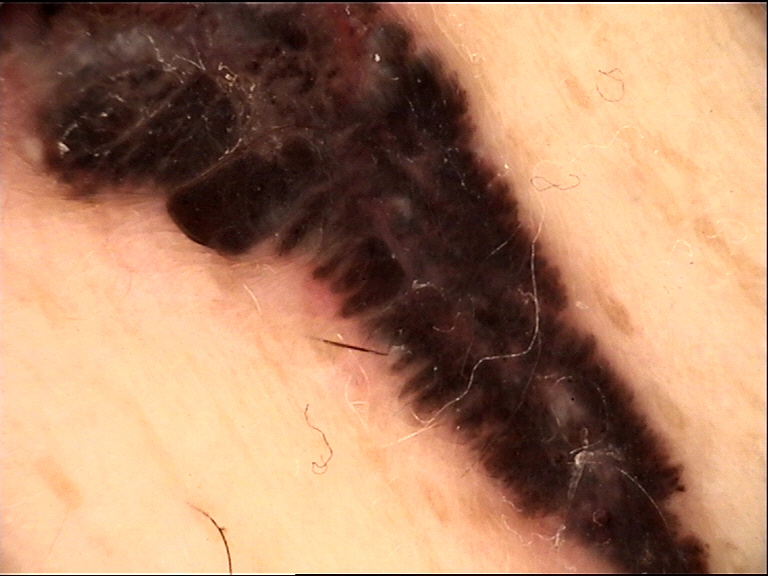Biopsy-confirmed as a basal cell carcinoma.